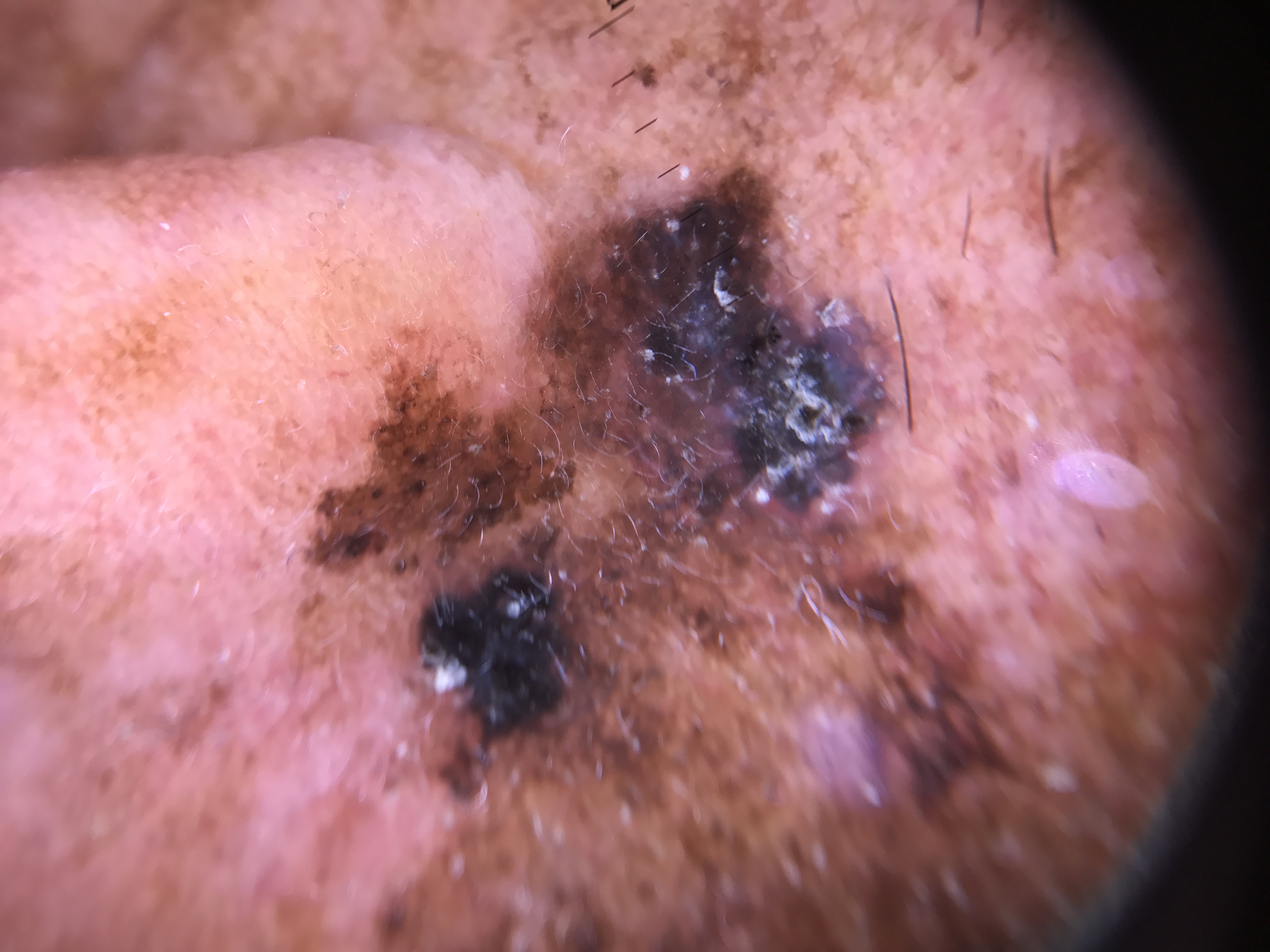Summary: A skin lesion imaged with a dermatoscope. Conclusion: The biopsy diagnosis was a lentigo maligna.